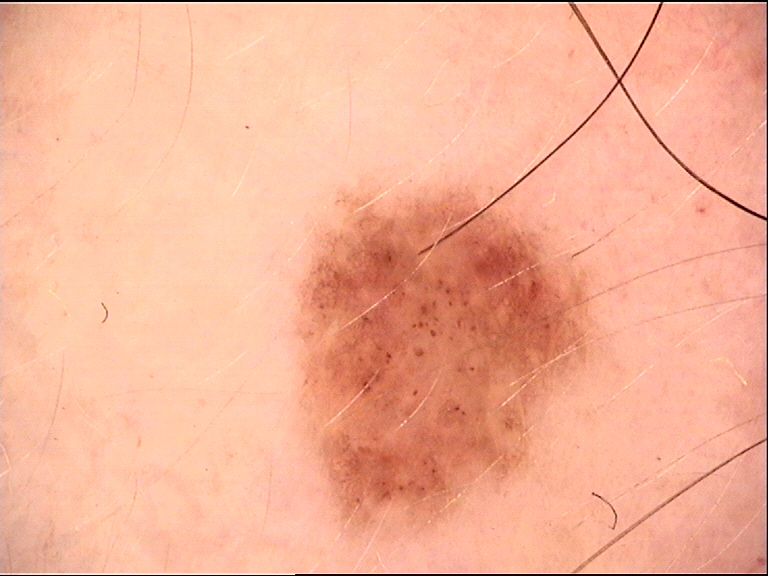The diagnosis was a dysplastic junctional nevus.